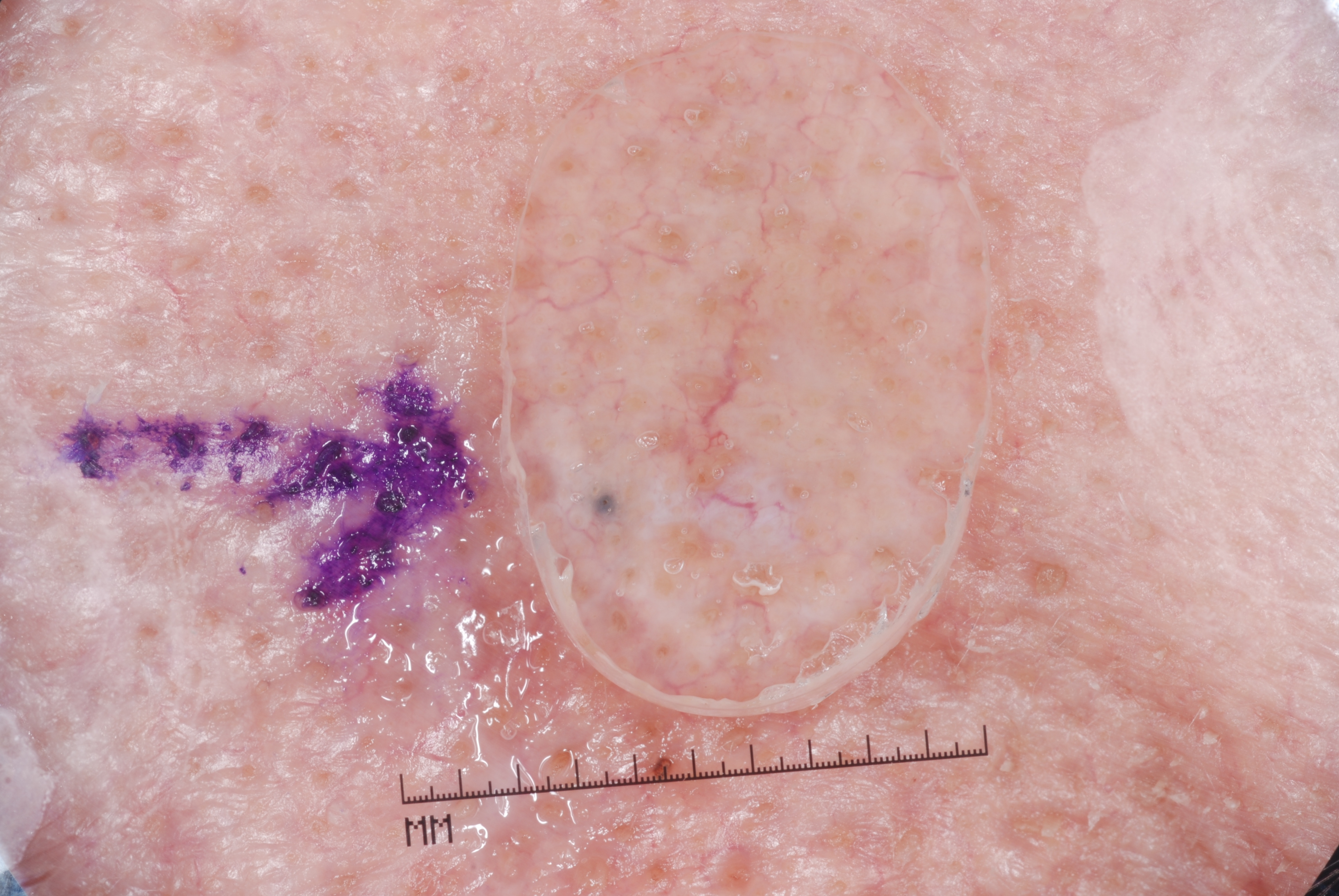patient = male, about 70 years old
imaging = dermoscopy of a skin lesion
lesion extent = ~11% of the field
features = milia-like cysts; absent: pigment network, streaks, and negative network
bounding box = <box>529, 254, 903, 673</box>
assessment = a melanocytic nevus